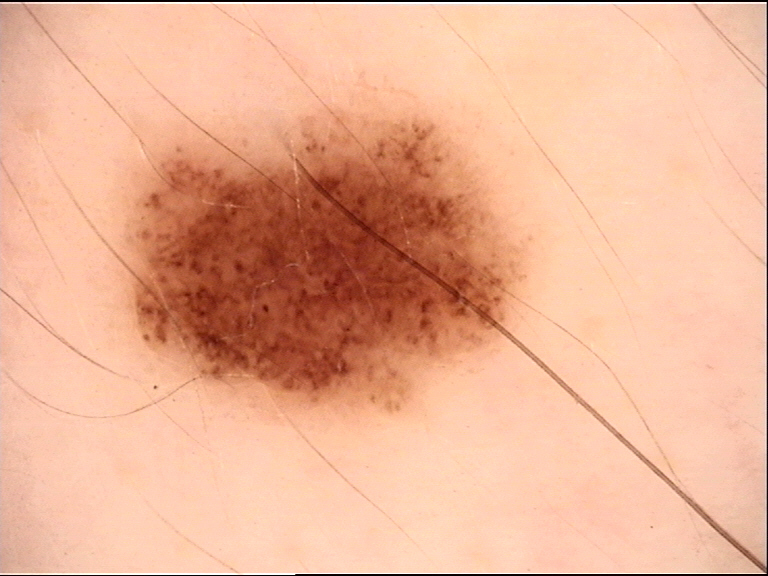{
  "image": "dermatoscopy",
  "diagnosis": {
    "name": "dysplastic compound nevus",
    "code": "cd",
    "malignancy": "benign",
    "super_class": "melanocytic",
    "confirmation": "expert consensus"
  }
}